A patient 81 years of age.
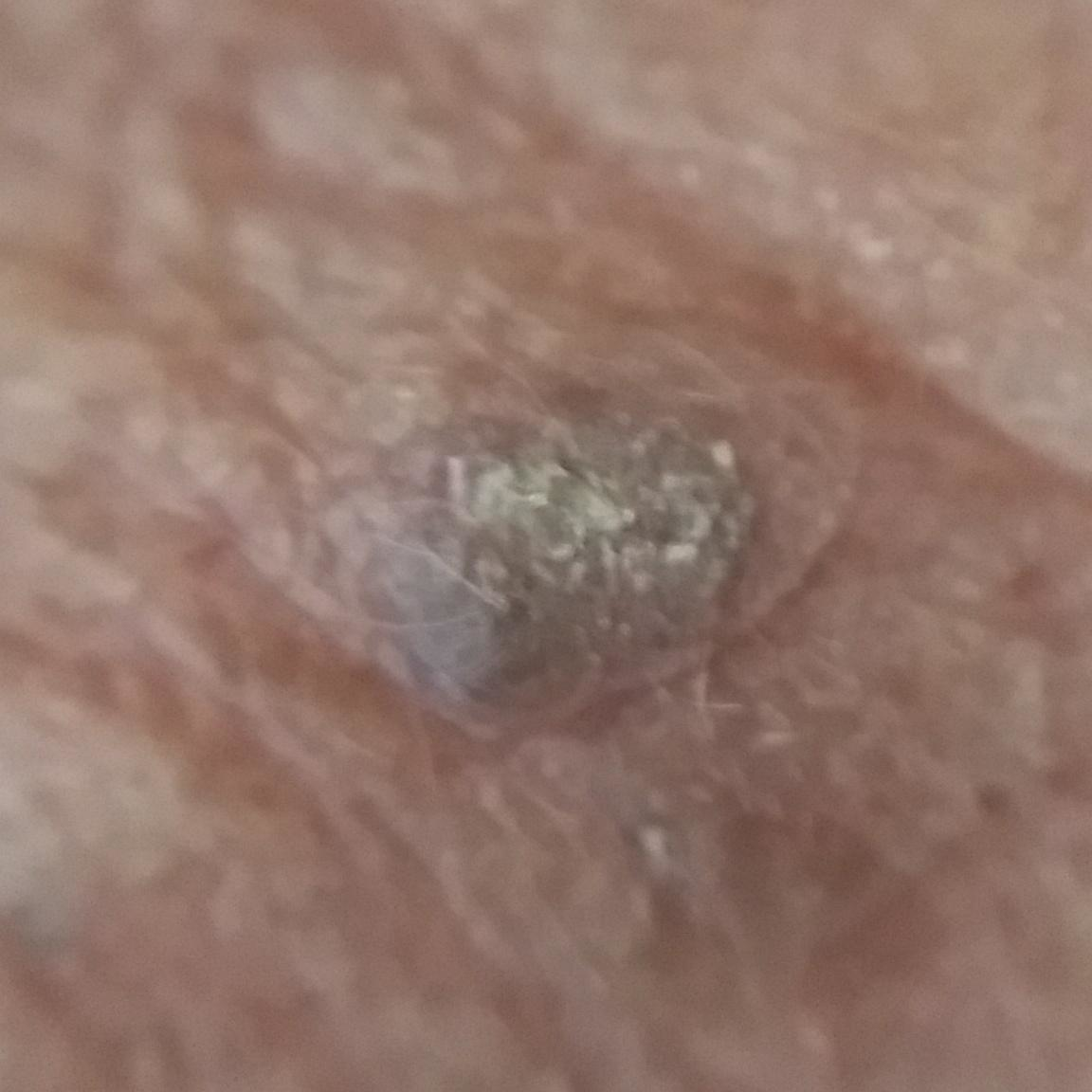symptoms:
  present:
    - elevation
diagnosis:
  name: seborrheic keratosis
  code: SEK
  malignancy: benign
  confirmation: clinical consensus